A skin lesion imaged with a dermatoscope.
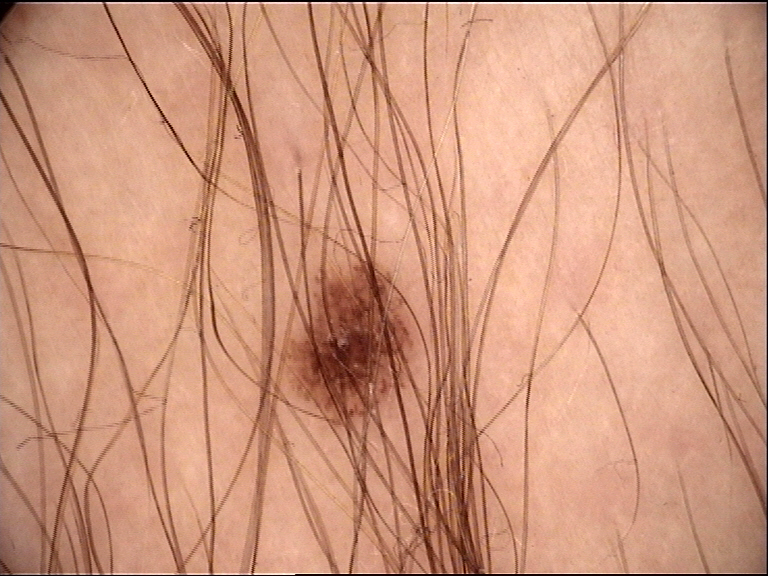Labeled as a dysplastic junctional nevus.